The subject is a female aged 30–39 · the contributor notes the lesion is rough or flaky and raised or bumpy · no relevant systemic symptoms · reported lesion symptoms include itching · present for less than one week · the patient considered this a rash · the affected area is the head or neck · close-up view: 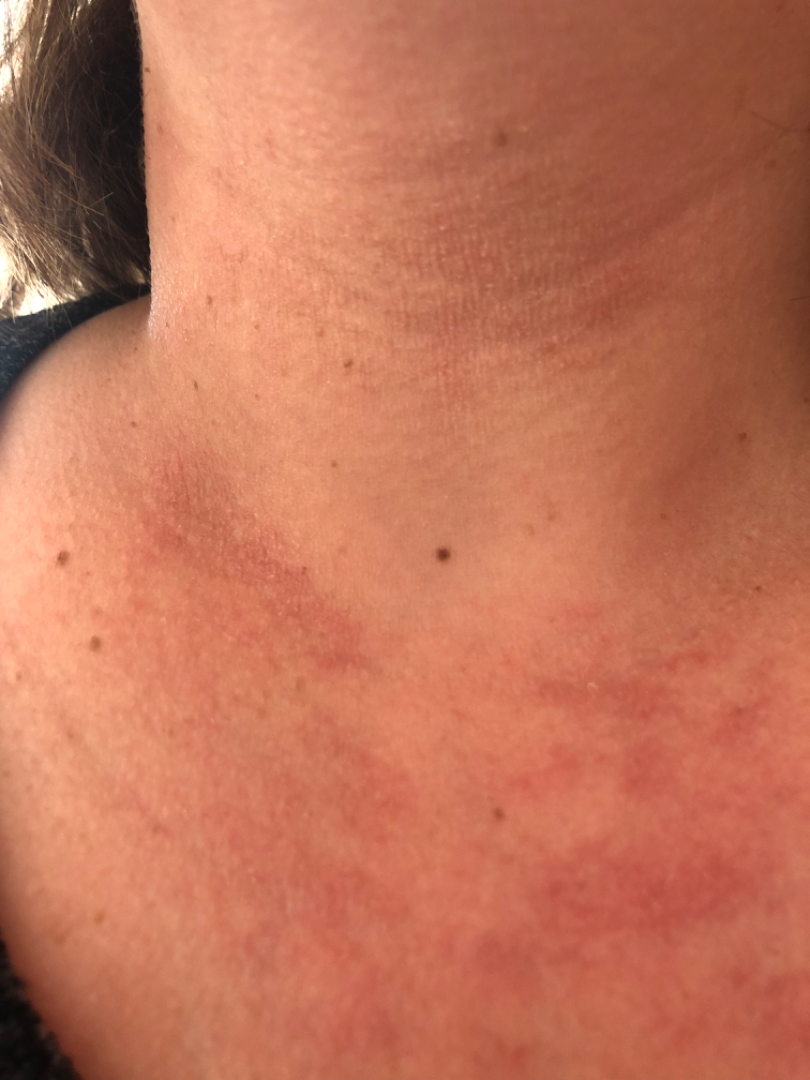<report>
  <differential>
    <tied_lead>Allergic Contact Dermatitis, Irritant Contact Dermatitis</tied_lead>
  </differential>
</report>